A dermatoscopic image of a skin lesion — 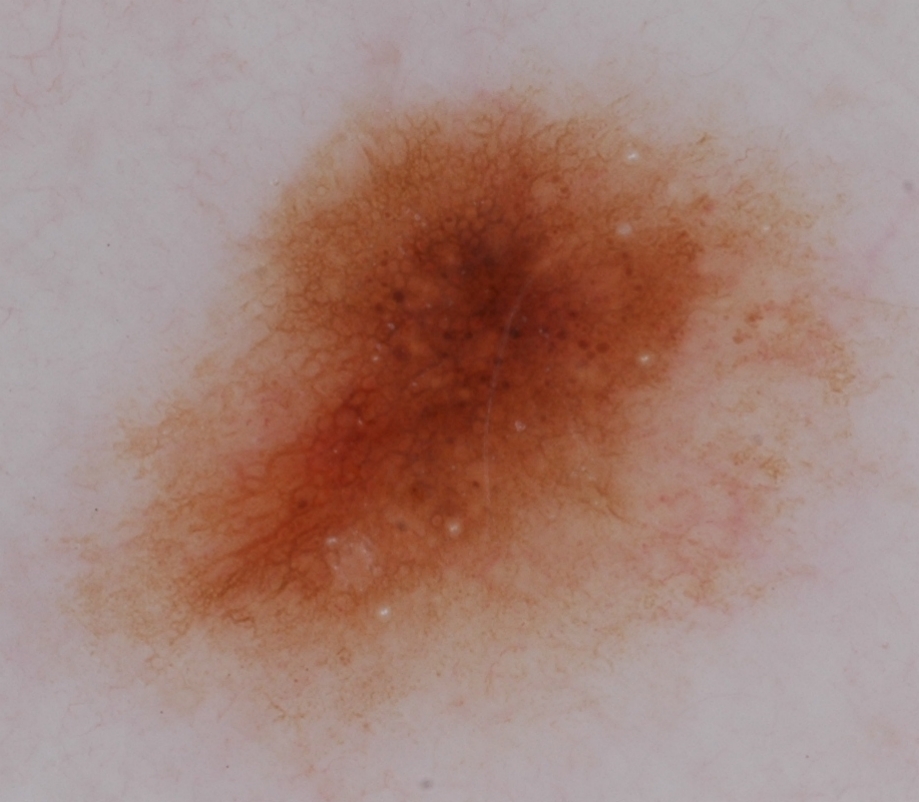| key | value |
|---|---|
| bounding box | x1=58 y1=80 x2=863 y2=747 |
| impression | a melanocytic nevus |